A moderate number of moles by the patient's own estimate · acquired for a research image collection, with no referral diagnosis · a female patient age 50:
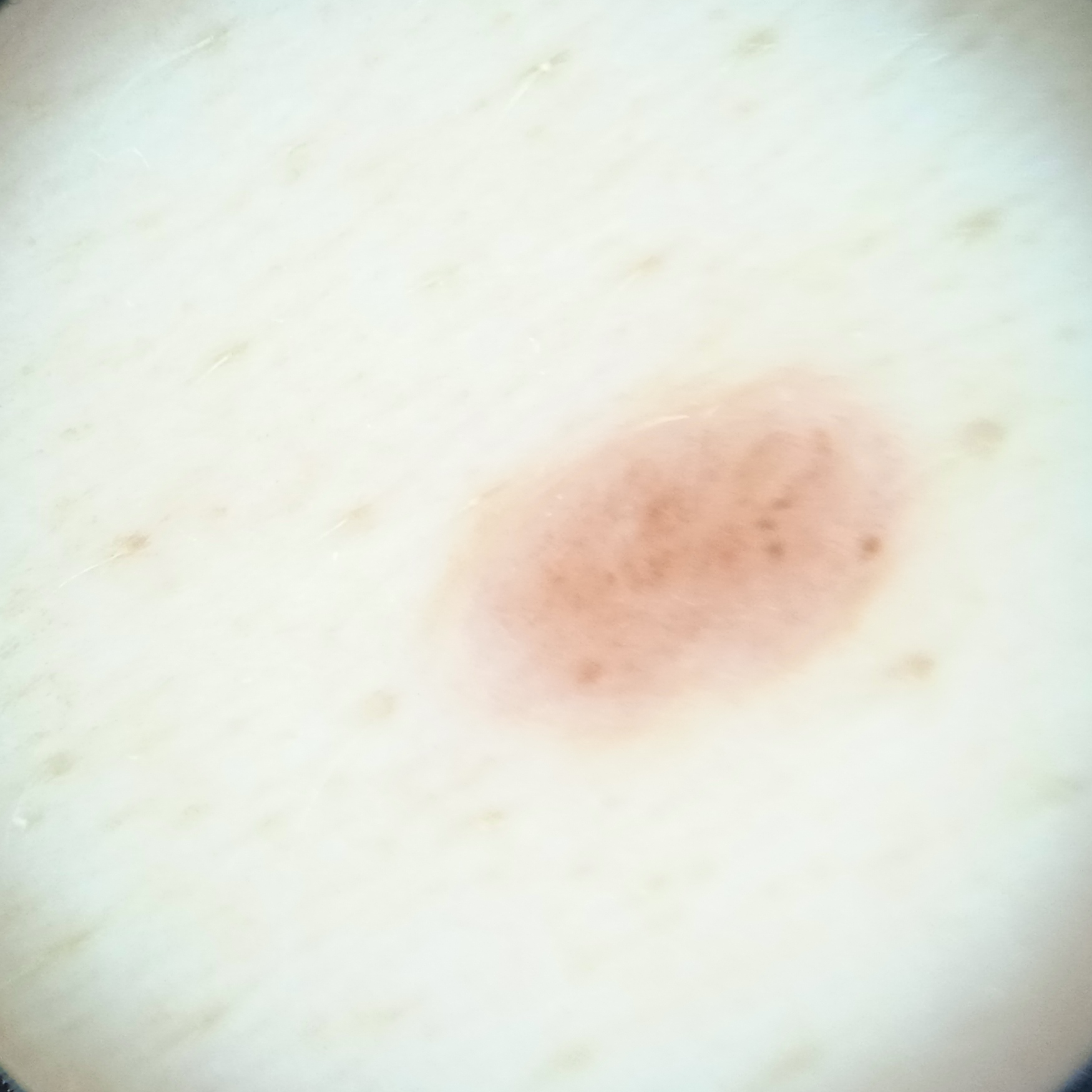site = the torso
diameter = 4.9 mm
diagnostic label = melanocytic nevus (dermatologist consensus)